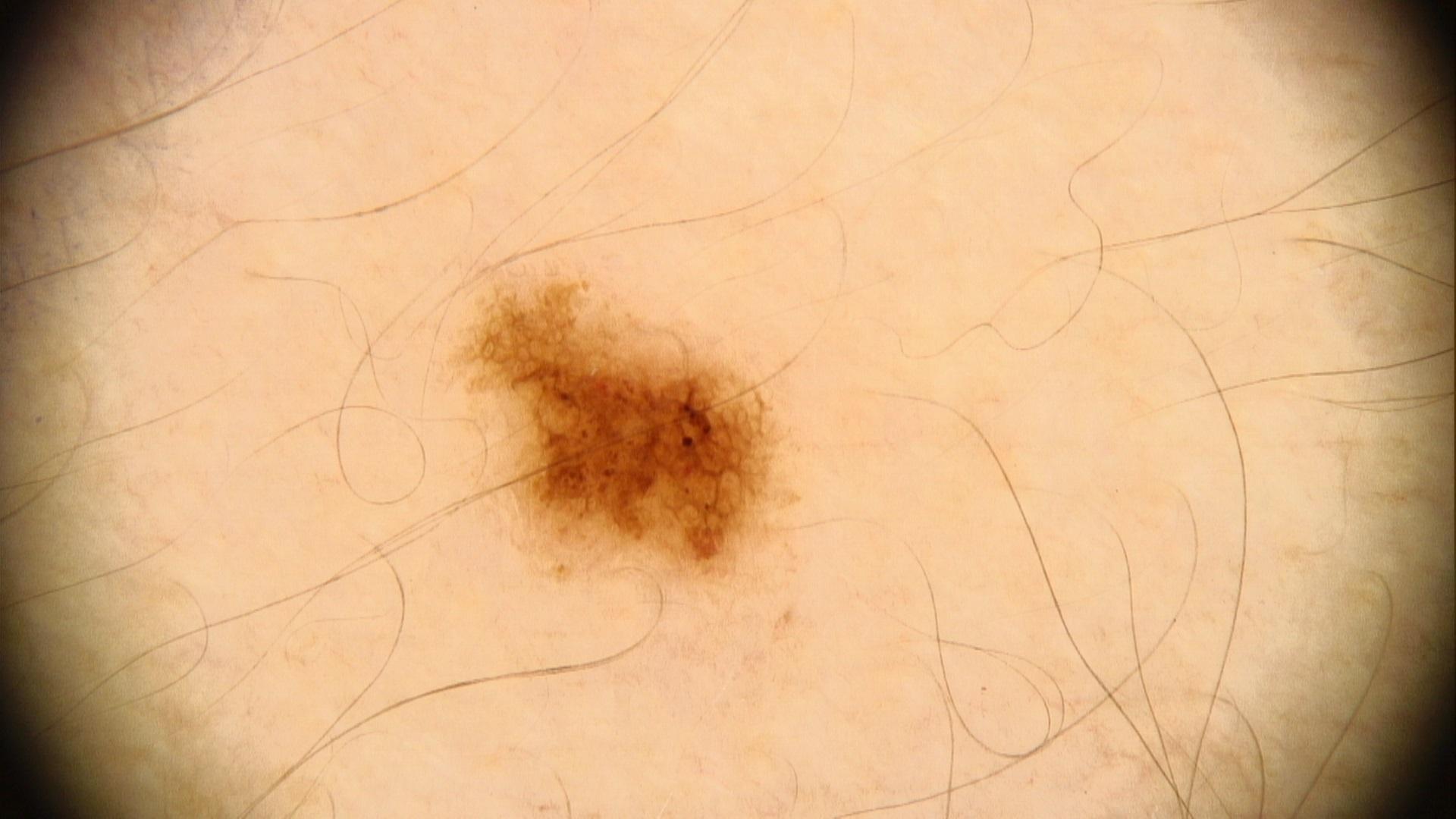The clinical assessment was a melanocytic lesion — a nevus.